A skin lesion imaged with a dermatoscope.
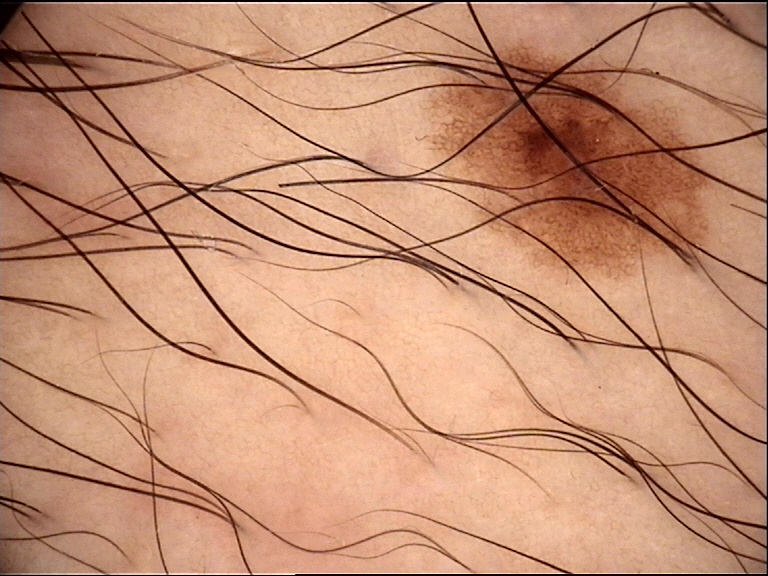assessment: dysplastic junctional nevus (expert consensus)